Self-categorized by the patient as a rash. The patient reports itching and darkening. The lesion is described as raised or bumpy and rough or flaky. The subject is a female aged 30–39. The condition has been present for less than one week. The lesion involves the arm. The photo was captured at an angle: 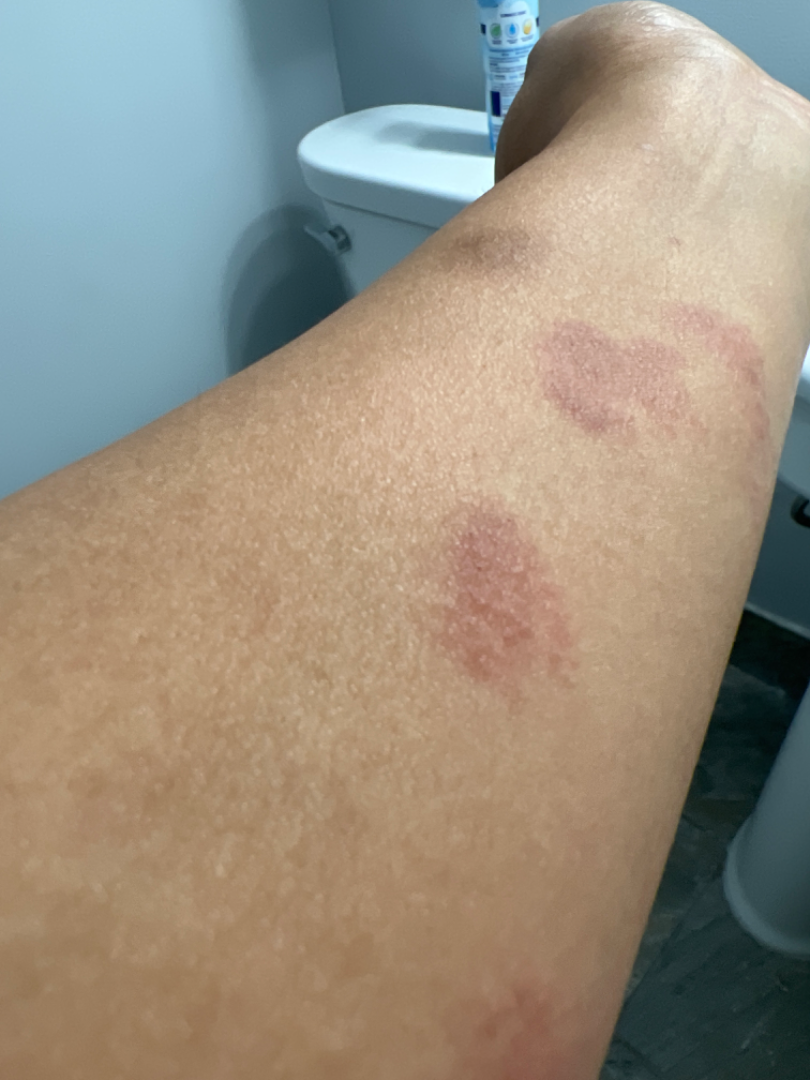The differential includes Eczema and Granuloma annulare, with no clear leading consideration; possibly Tinea; an alternative is Erythema elevatum diutinum; less likely is Allergic Contact Dermatitis.